This is a dermoscopic photograph of a skin lesion · a male subject, in their mid- to late 70s — 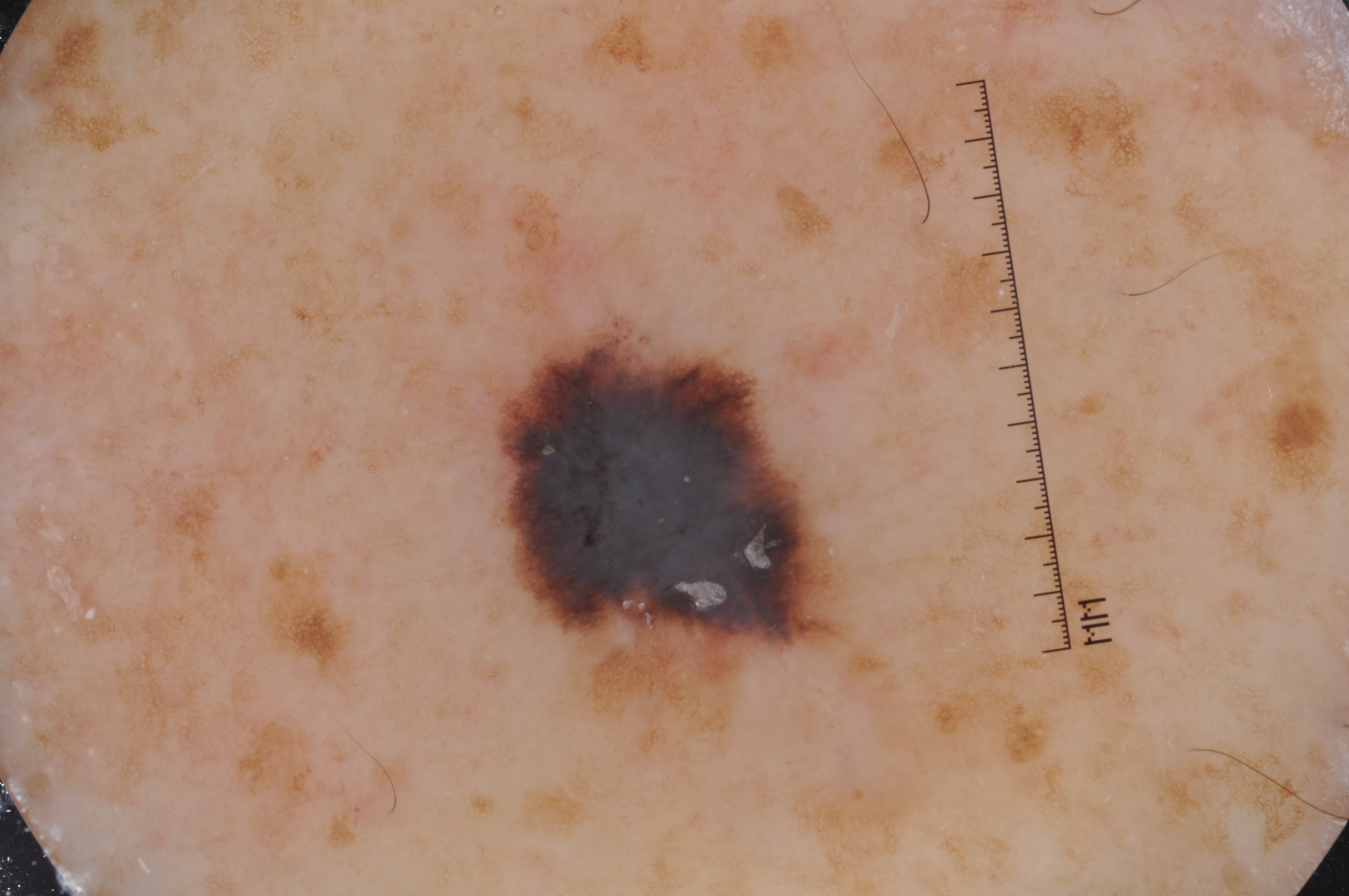| key | value |
|---|---|
| bounding box | 497, 333, 828, 649 |
| dermoscopic findings | pigment network and milia-like cysts |
| diagnosis | a melanoma, a malignant skin lesion |